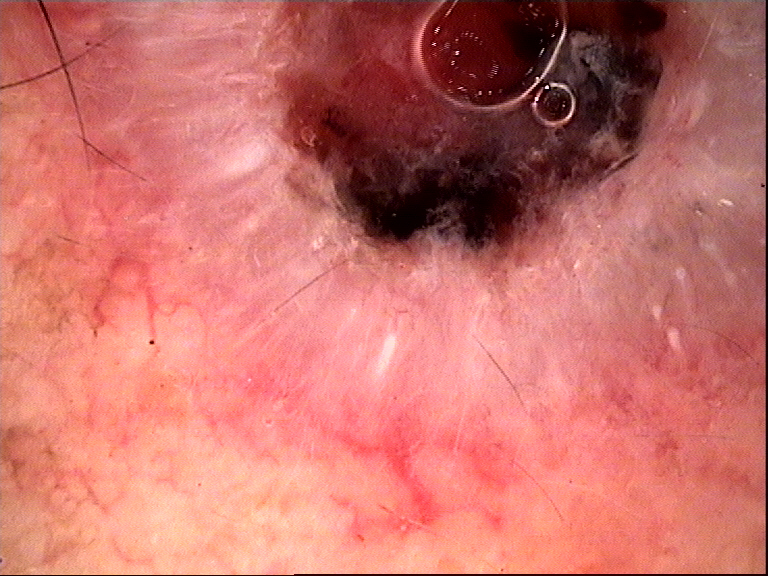{
  "image": "dermatoscopy",
  "diagnosis": {
    "name": "basal cell carcinoma",
    "code": "bcc",
    "malignancy": "malignant",
    "super_class": "non-melanocytic",
    "confirmation": "histopathology"
  }
}